A dermoscopic photograph of a skin lesion.
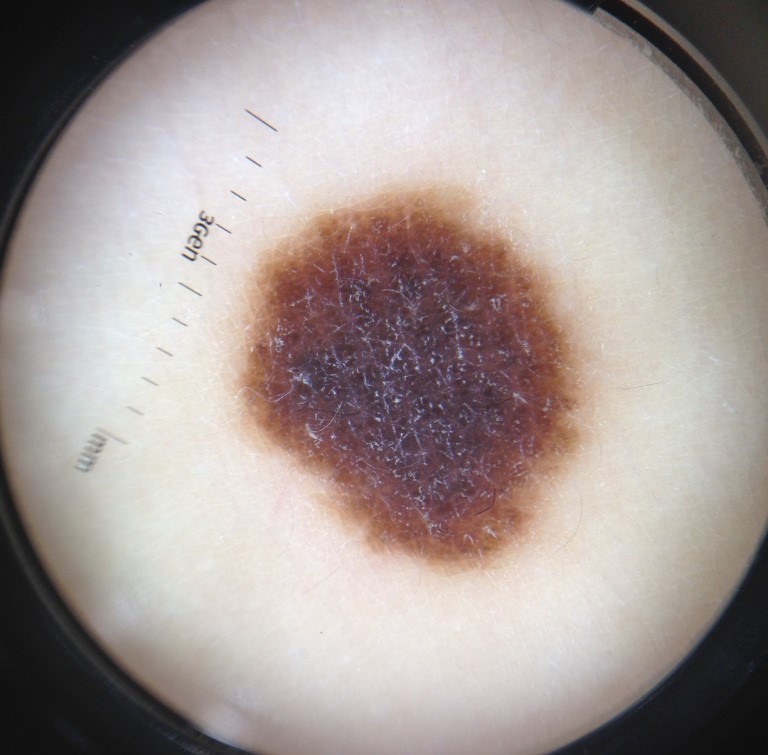Q: What is the diagnosis?
A: congenital compound nevus (expert consensus)